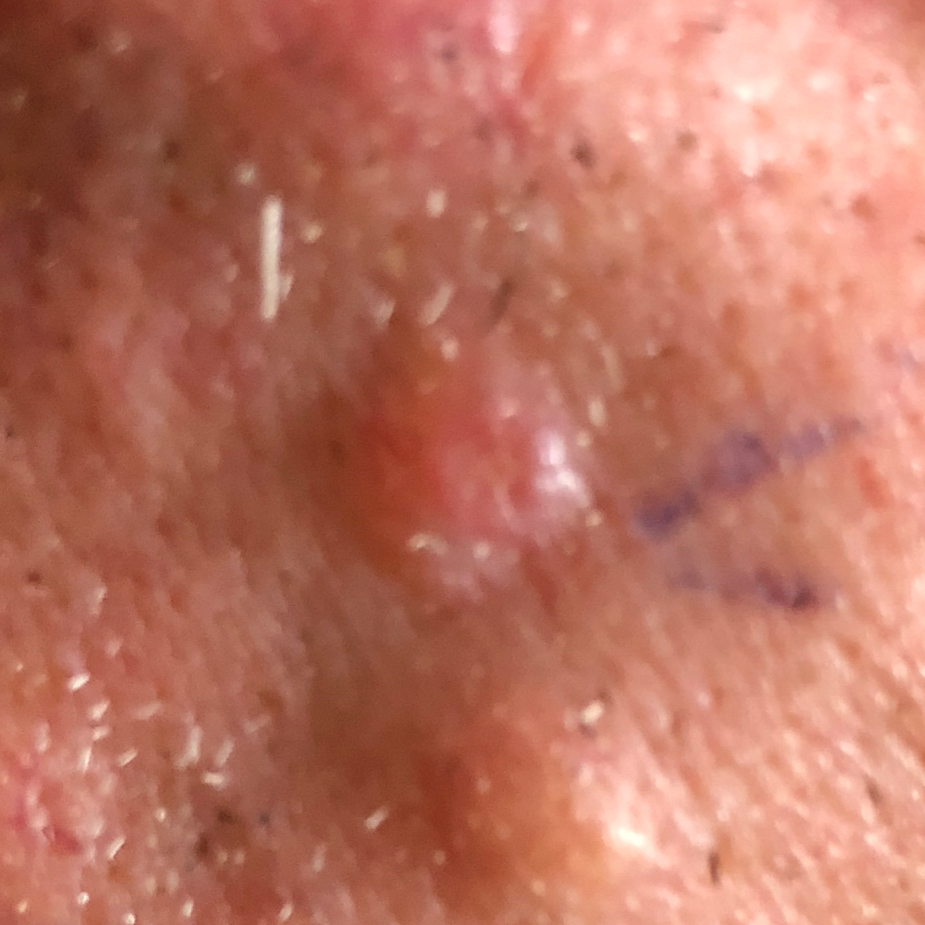| feature | finding |
|---|---|
| risk factors | prior malignancy (patient or family), prior skin cancer (patient or family), alcohol use, pesticide exposure |
| patient | male, aged 65 |
| lesion size | 7x5 mm |
| reported symptoms | elevation, growth |
| diagnostic label | basal cell carcinoma (biopsy-proven) |